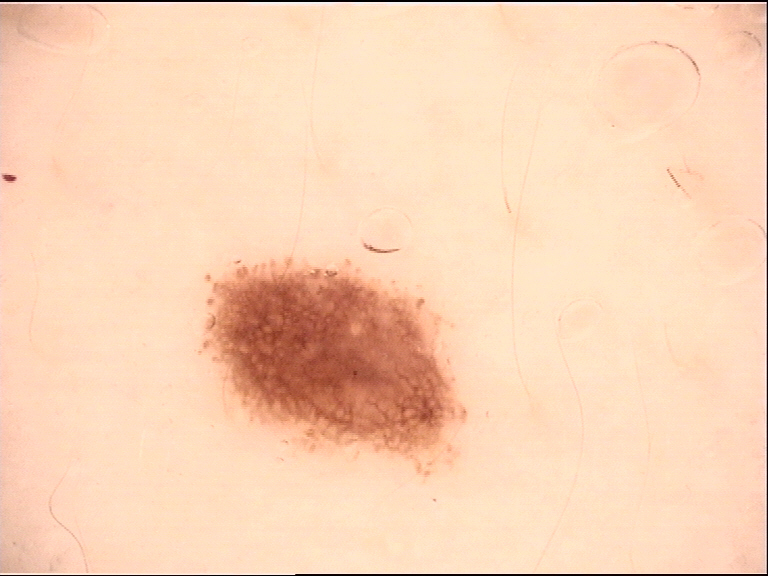A dermoscopy image of a single skin lesion. Consistent with a benign lesion — a dysplastic junctional nevus.